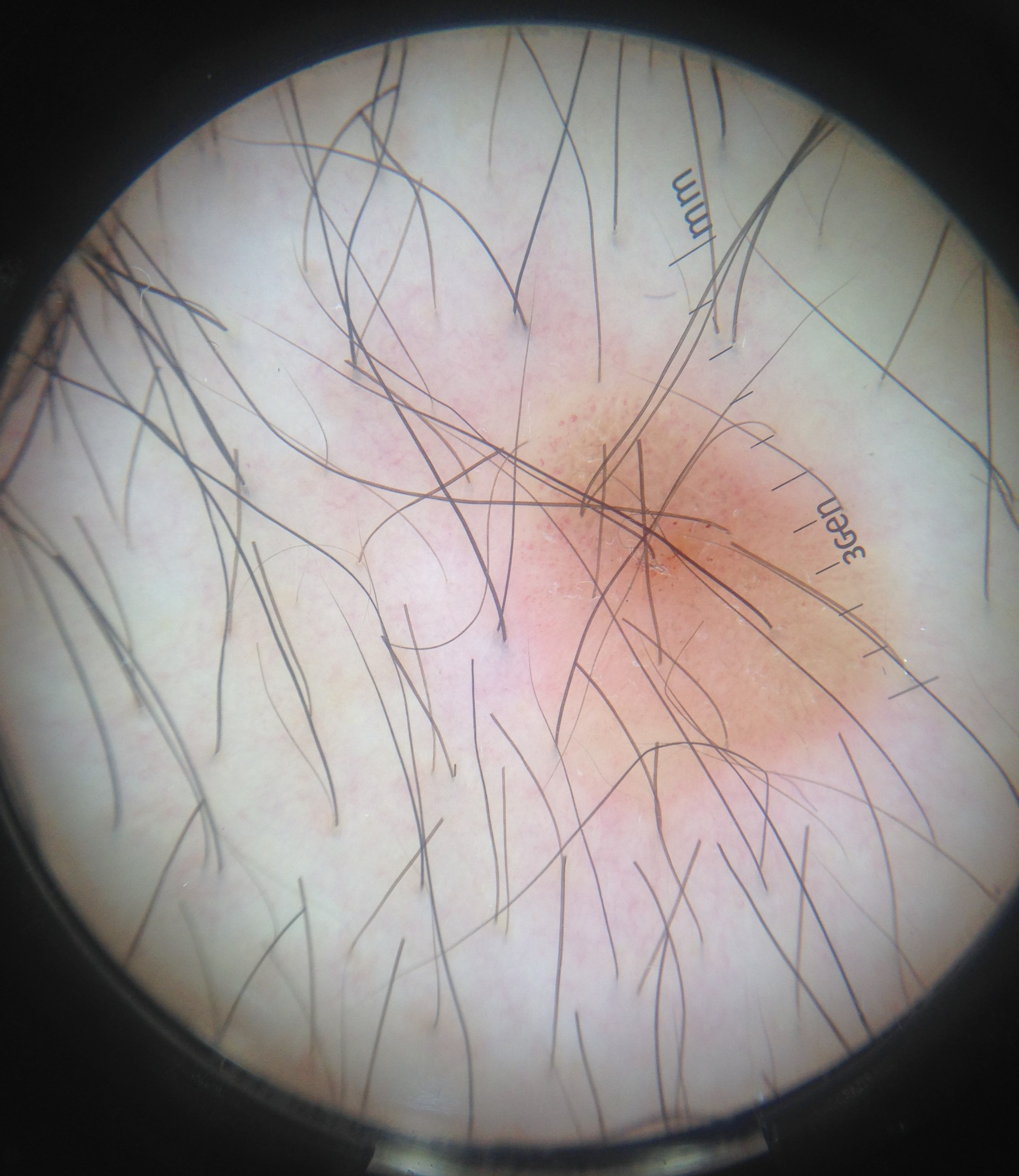{"lesion_type": {"main_class": "keratinocytic"}, "diagnosis": {"name": "seborrheic keratosis", "code": "sk", "malignancy": "benign", "super_class": "non-melanocytic", "confirmation": "expert consensus"}}